The front of the torso, arm and back of the torso are involved · this is a close-up image — 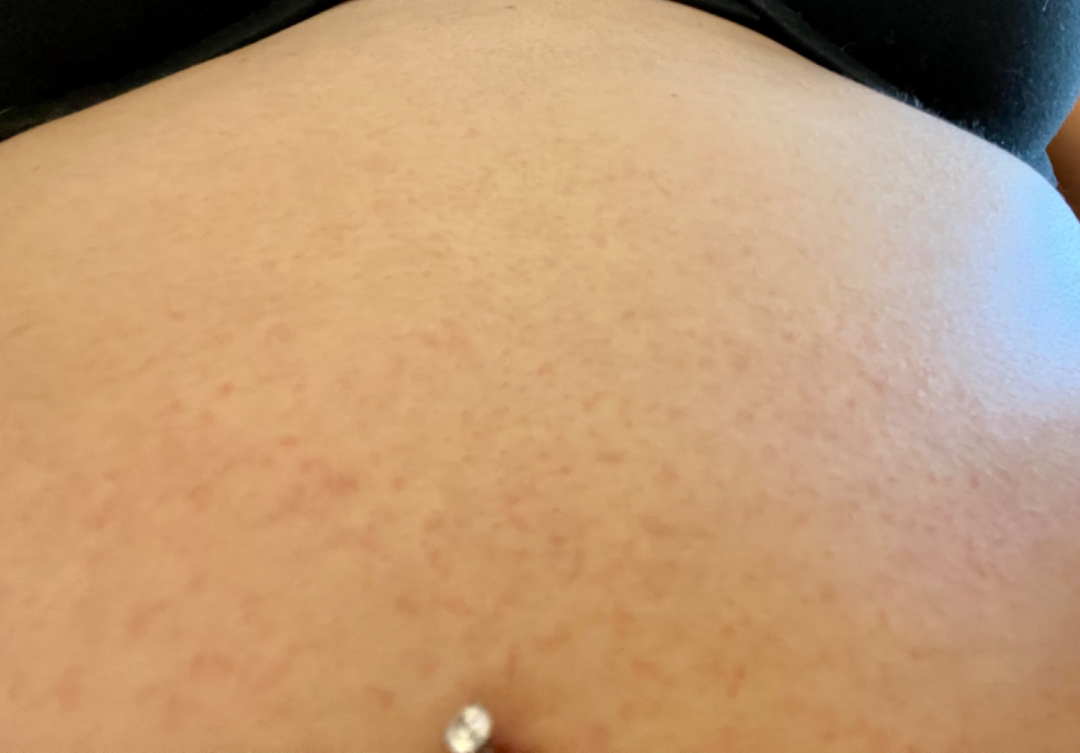assessment=not assessable